Female contributor, age 50–59; an image taken at an angle; the lesion involves the leg:
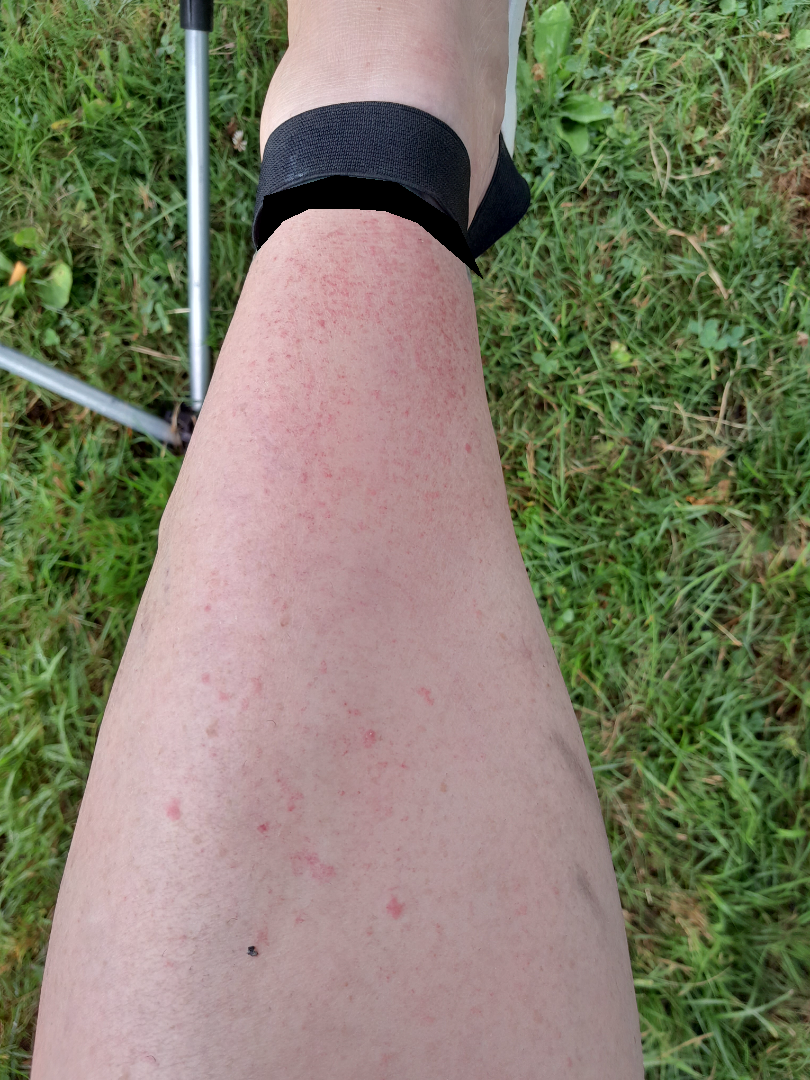  assessment: indeterminate
  duration: less than one week
  patient_category: a rash
  texture: raised or bumpy
  symptoms:
    - pain
    - burning
    - enlargement
    - itching